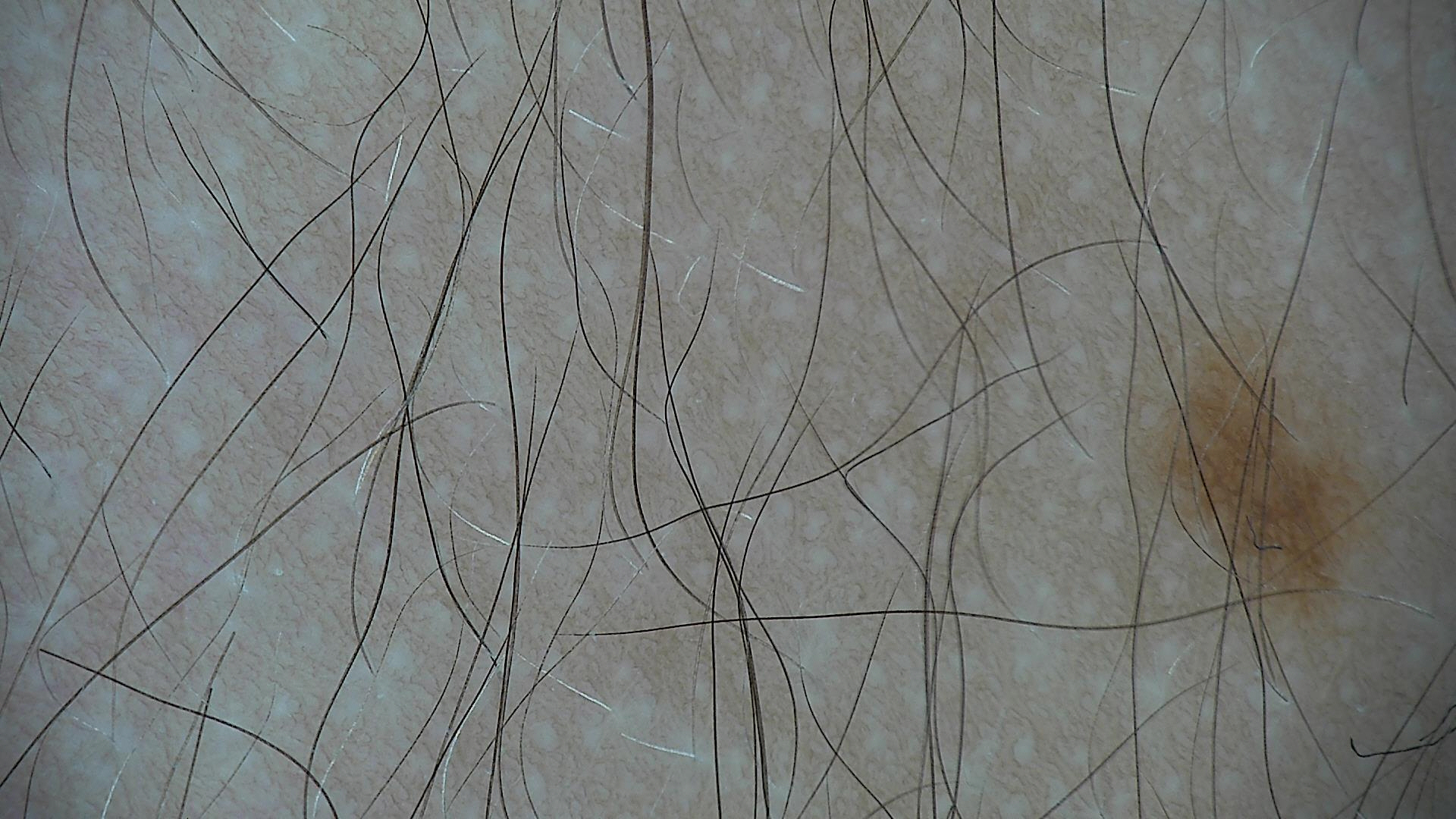Classified as a dysplastic junctional nevus.